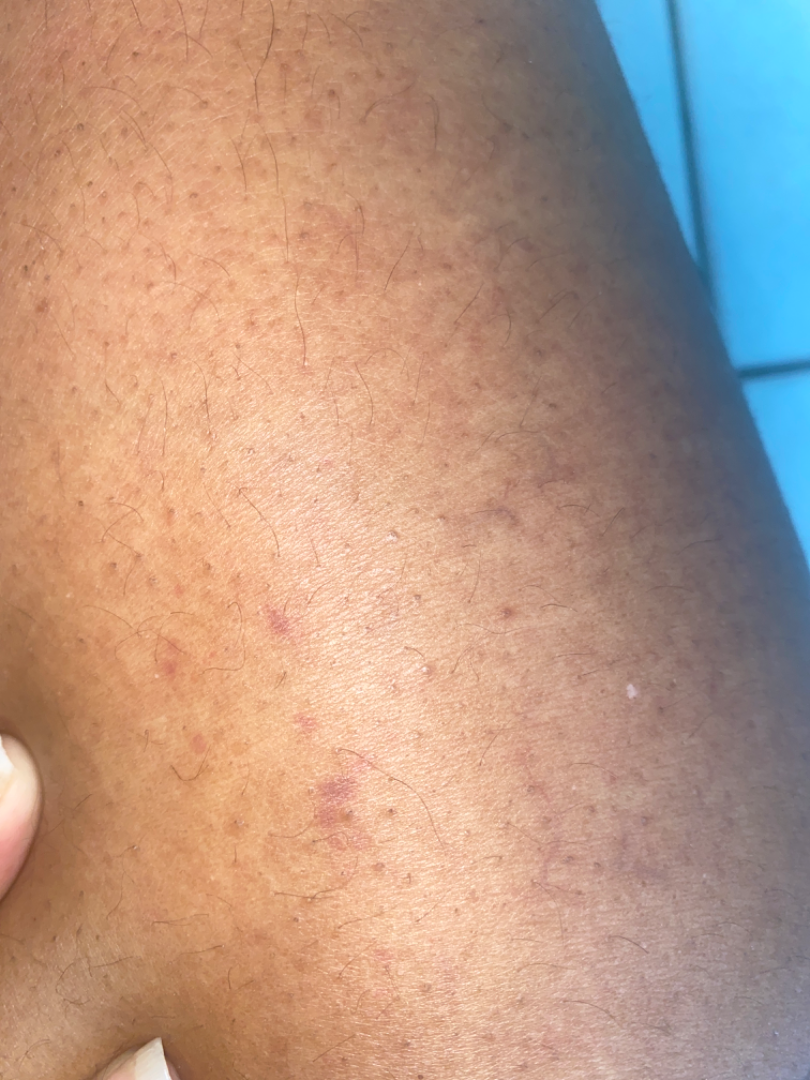Review:
The case was difficult to assess from the available photograph.
Patient information:
The lesion involves the leg. Reported duration is one to four weeks. Texture is reported as flat. The photograph is a close-up of the affected area.